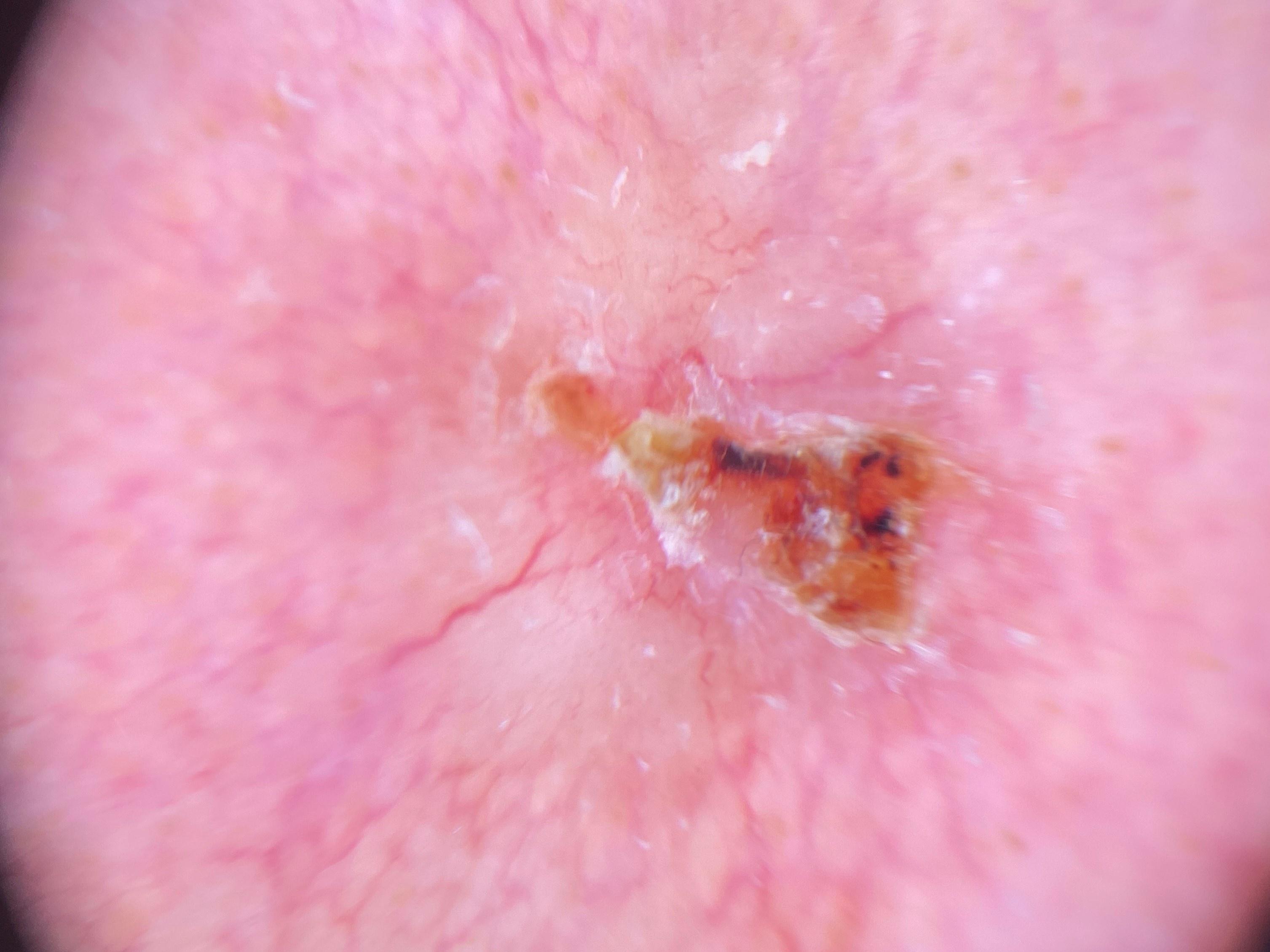modality = dermatoscopic image | risk factors = a prior melanoma | patient = male, in their 80s | pathology = Basal cell carcinoma (biopsy-proven).